The front of the torso, arm, head or neck, leg and back of the torso are involved; the photograph is a close-up of the affected area — 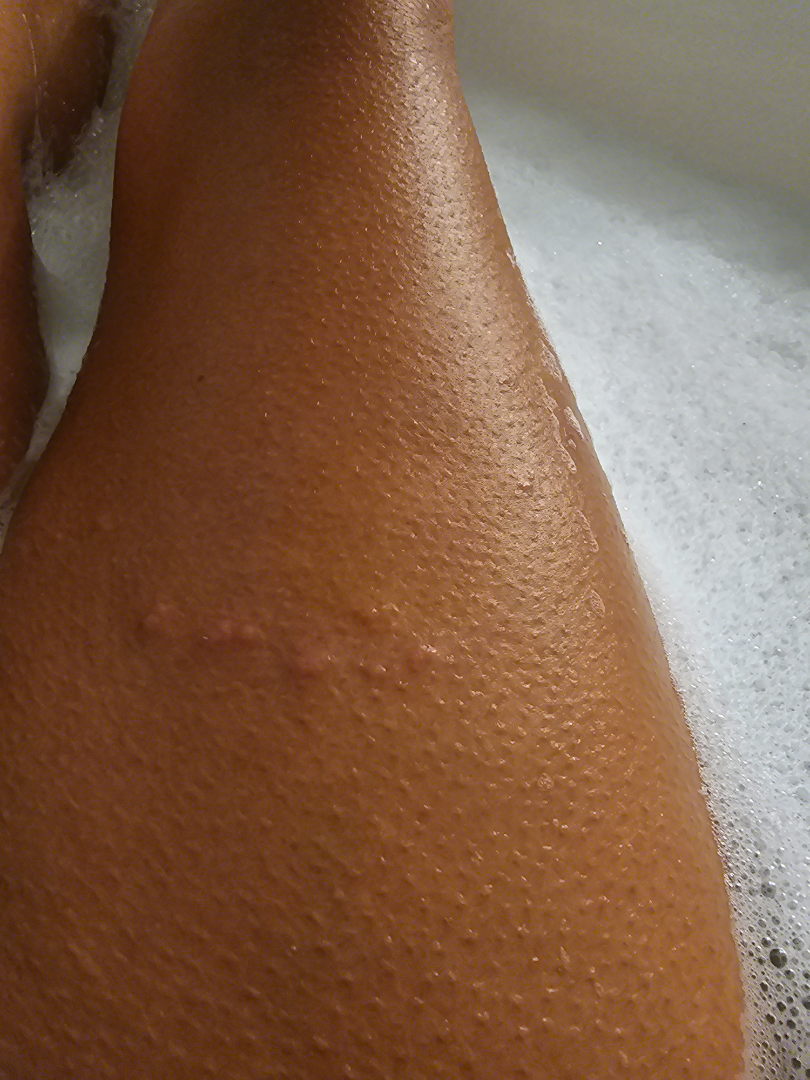Assessment:
One reviewing dermatologist: most likely Verruca vulgaris; also consider SK/ISK; the differential also includes Molluscum Contagiosum.